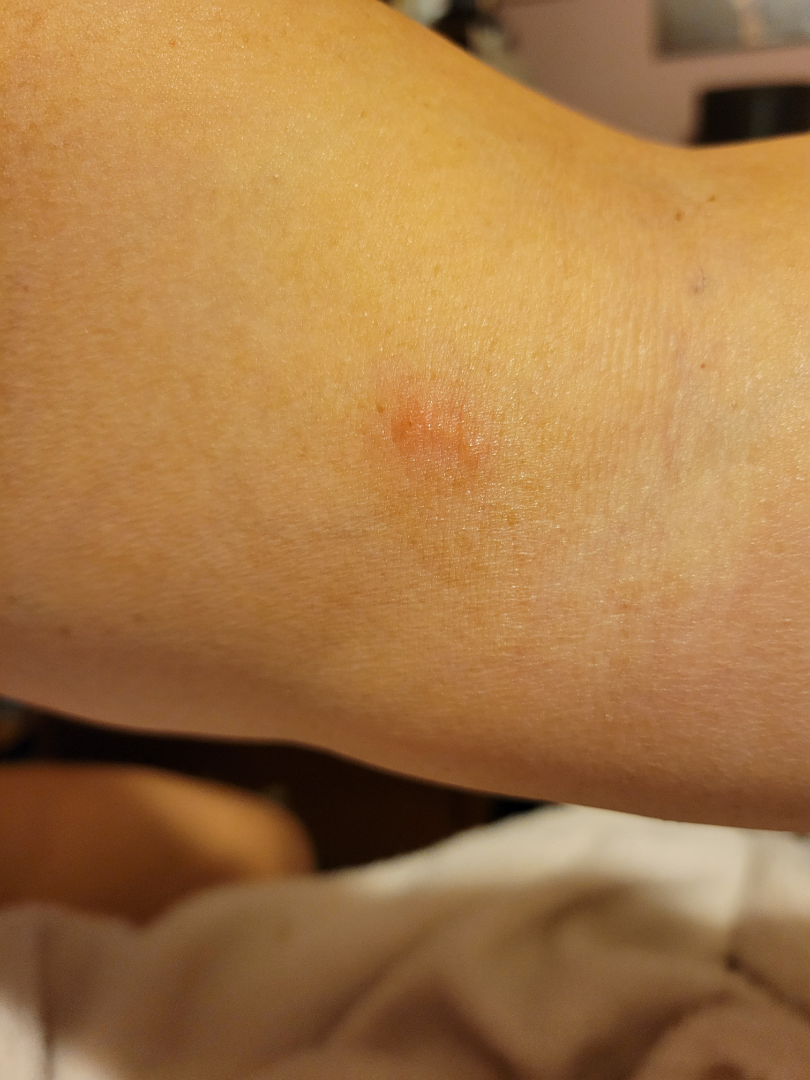Patient information: The patient also reports fatigue. The lesion is described as raised or bumpy. The contributor is female. The photo was captured at an angle. The affected area is the leg and arm. Reported lesion symptoms include itching and burning. Present for less than one week. The patient described the issue as a rash. Review: On remote dermatologist review, the differential, in no particular order, includes Folliculitis and Insect Bite; less likely is Allergic Contact Dermatitis; less probable is Herpes Simplex.